The lesion involves the leg; this image was taken at an angle; female subject, age 50–59 — 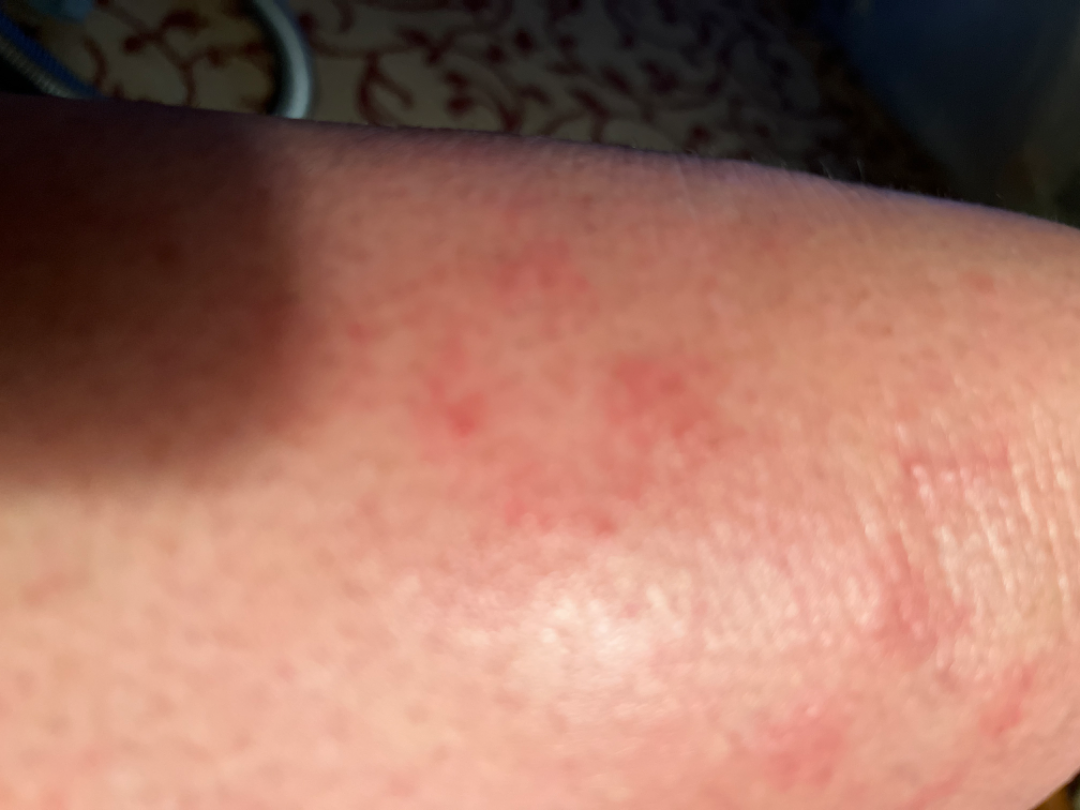dermatologist impression: most consistent with Eczema.